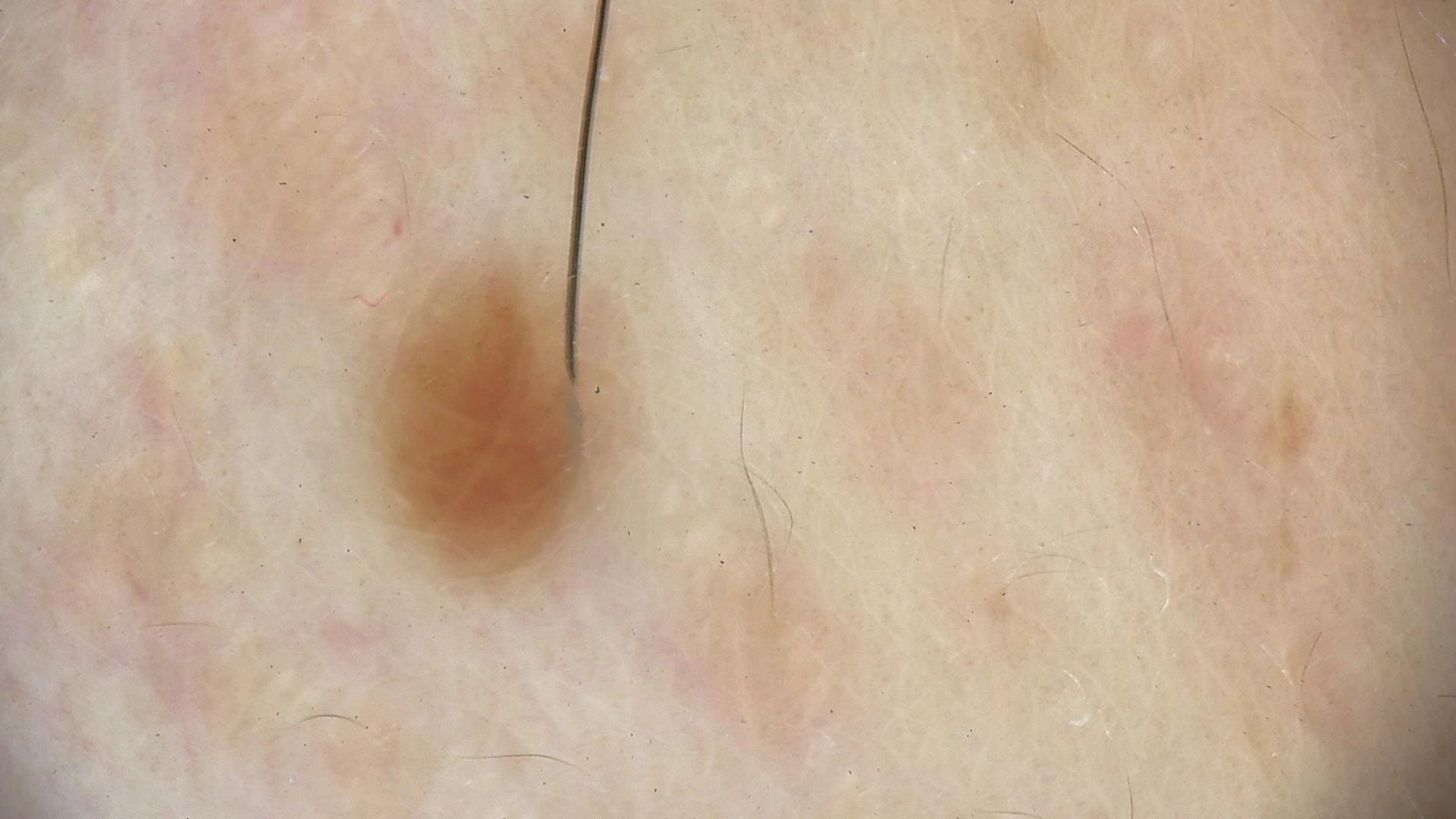A dermoscopy image of a single skin lesion. Labeled as a banal lesion — a dermal nevus.